The leg is involved. Female patient, age 18–29. An image taken at an angle — 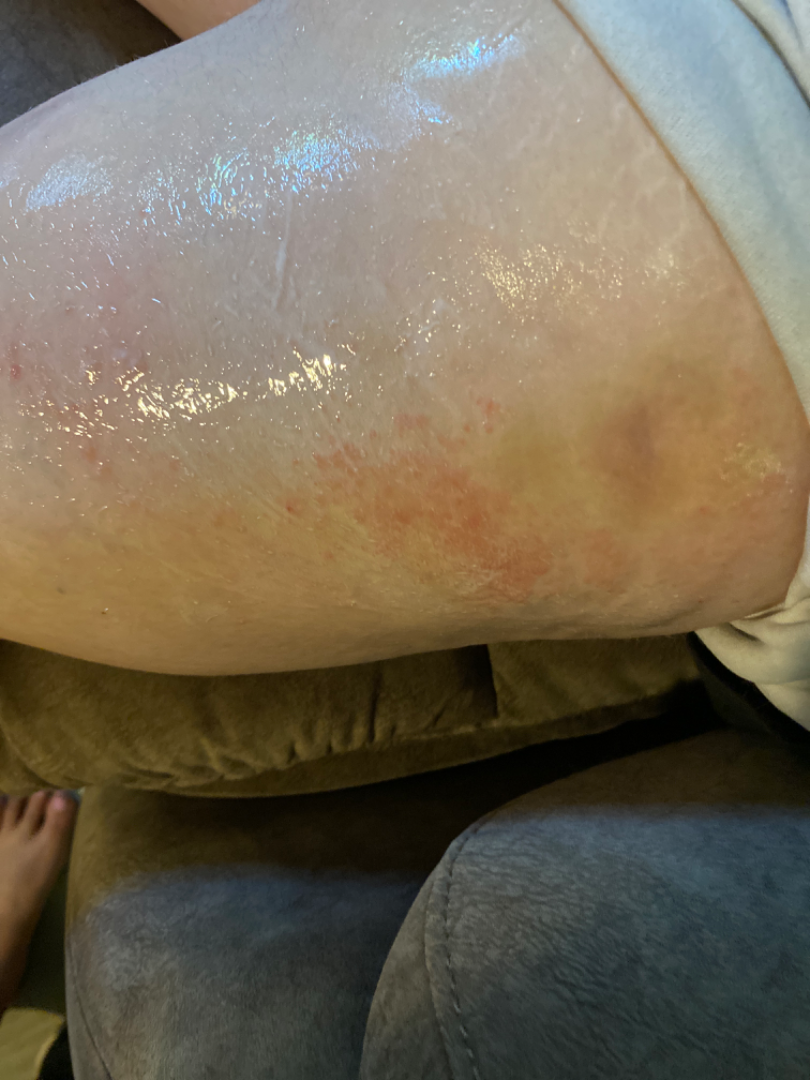Three dermatologists independently reviewed the case: most consistent with Eczema; an alternative is Contact dermatitis; a more distant consideration is Allergic Contact Dermatitis; less likely is Darier's disease; less probable is Hailey Hailey disease.